A subject aged 57; a clinical close-up photograph of a skin lesion: 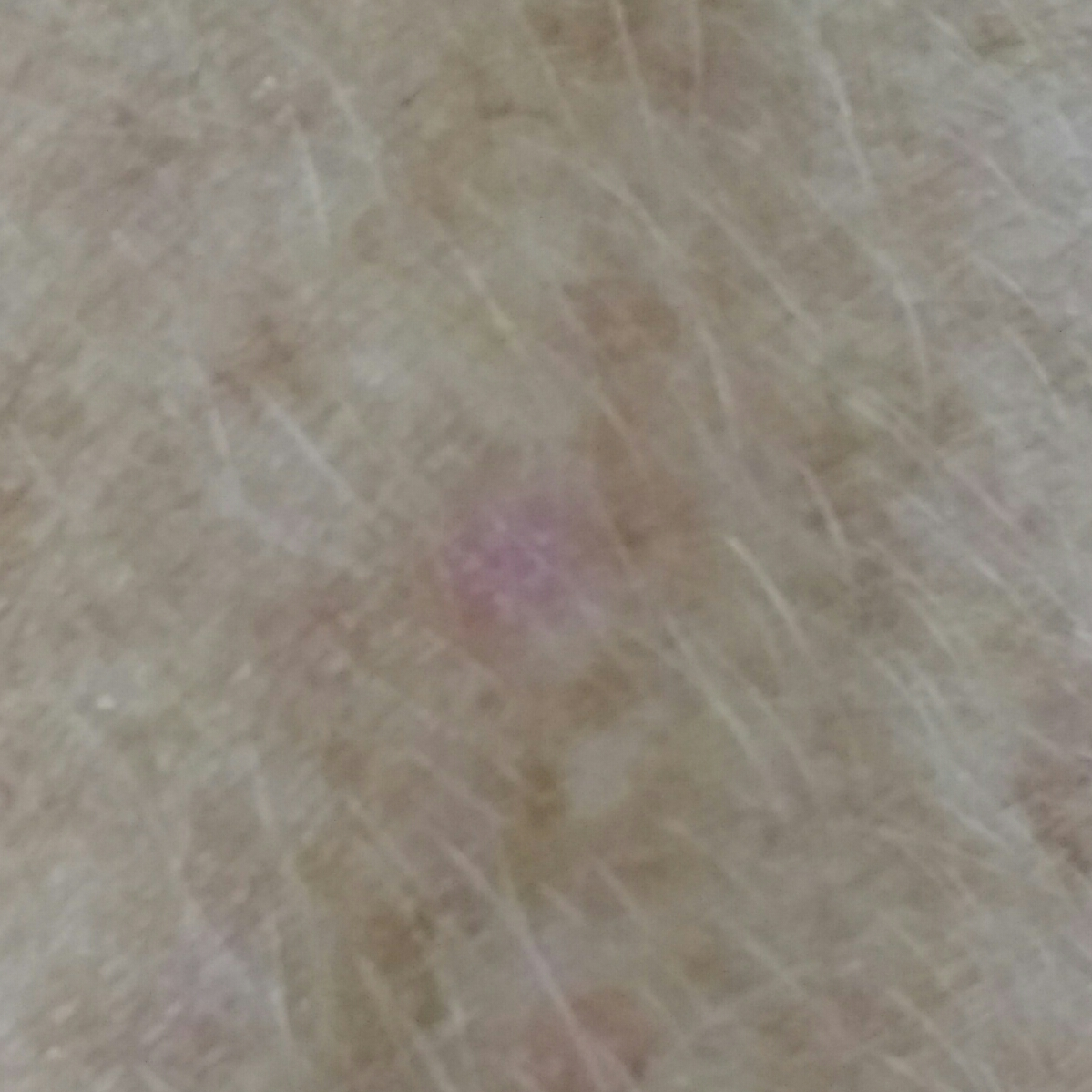| key | value |
|---|---|
| anatomic site | a forearm |
| symptoms | none reported |
| impression | actinic keratosis (clinical consensus) |